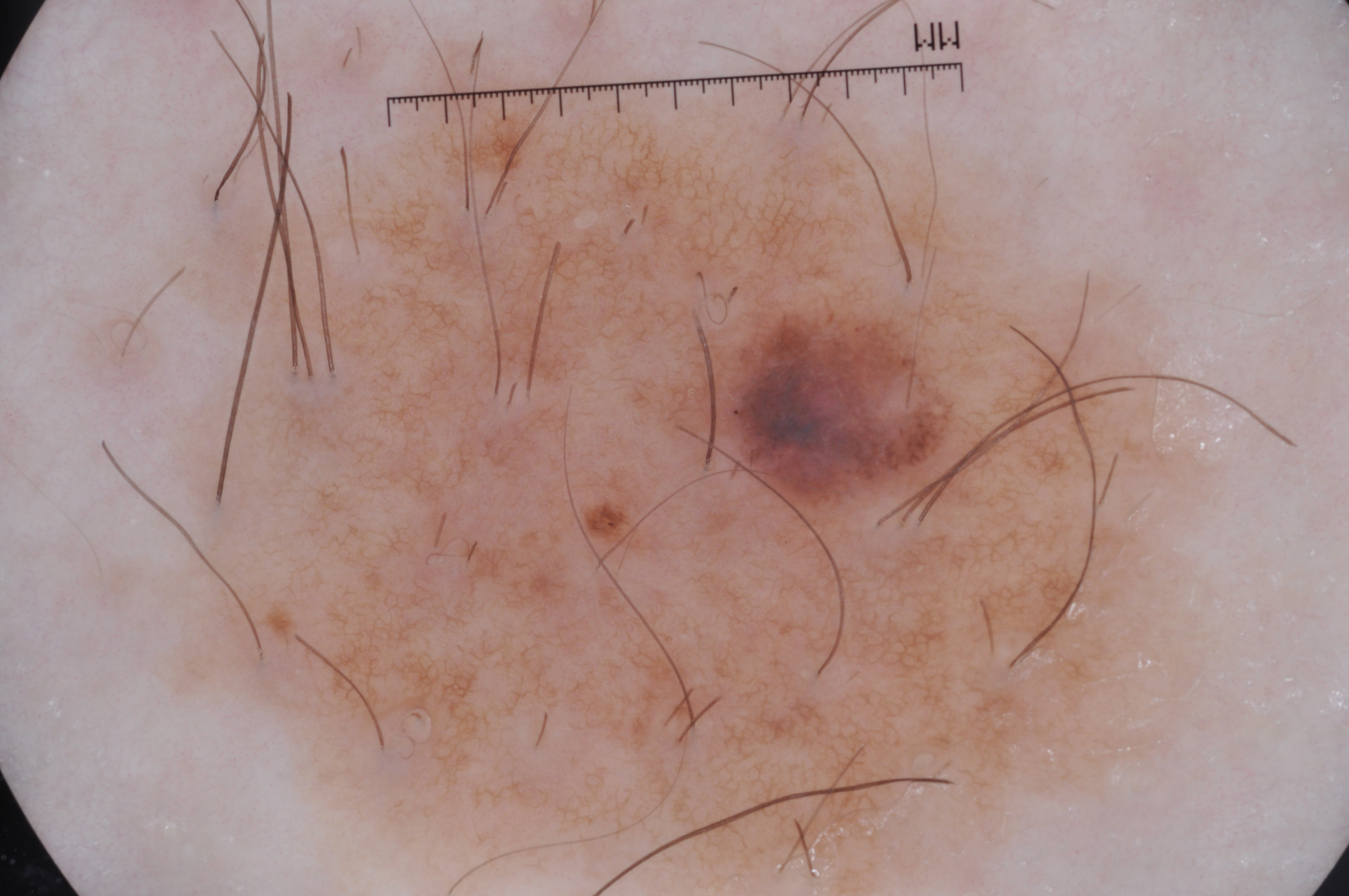image: dermoscopy of a skin lesion | patient: female, aged 38 to 42 | dermoscopic pattern: pigment network | lesion margin: extends past the field edge | bounding box: <box>169, 28, 1212, 895</box> | diagnostic label: a melanocytic nevus.